A clinical photo of a skin lesion taken with a smartphone. A male subject aged 56 — 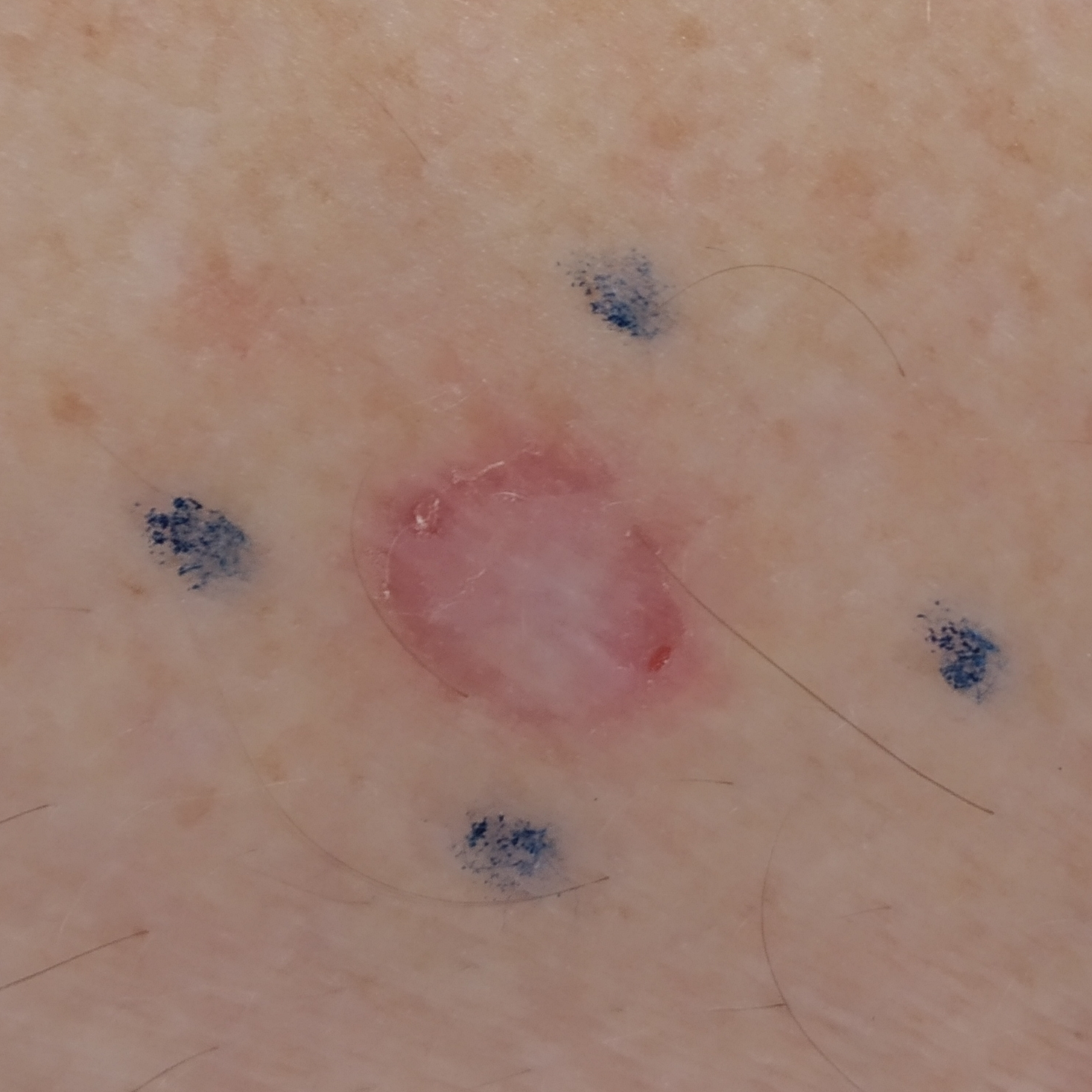Case summary:
Per patient report, the lesion is elevated and has grown.
Diagnosis:
Histopathologically confirmed as a basal cell carcinoma.